The lesion is described as rough or flaky · located on the head or neck · symptoms reported: enlargement and itching · self-categorized by the patient as a rash · the photograph is a close-up of the affected area · the patient also reports fatigue and joint pain · the patient notes the condition has been present for one to four weeks: 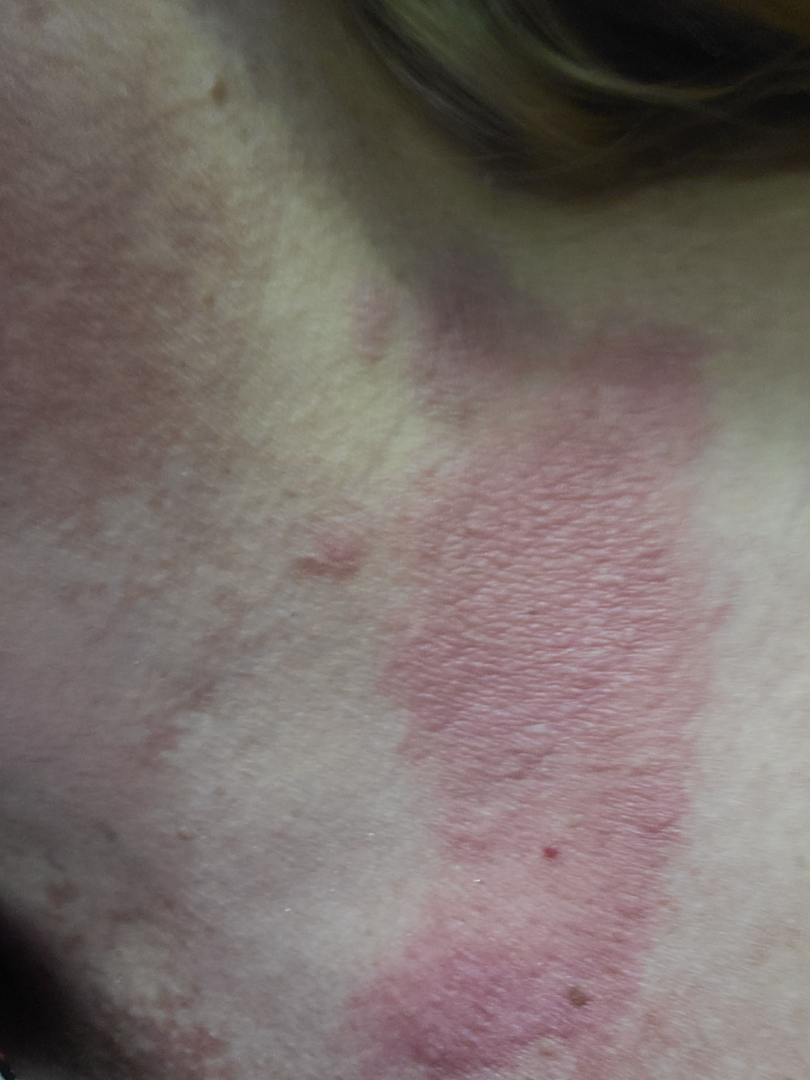Review:
The condition could not be reliably identified from the image.